Close-up view.
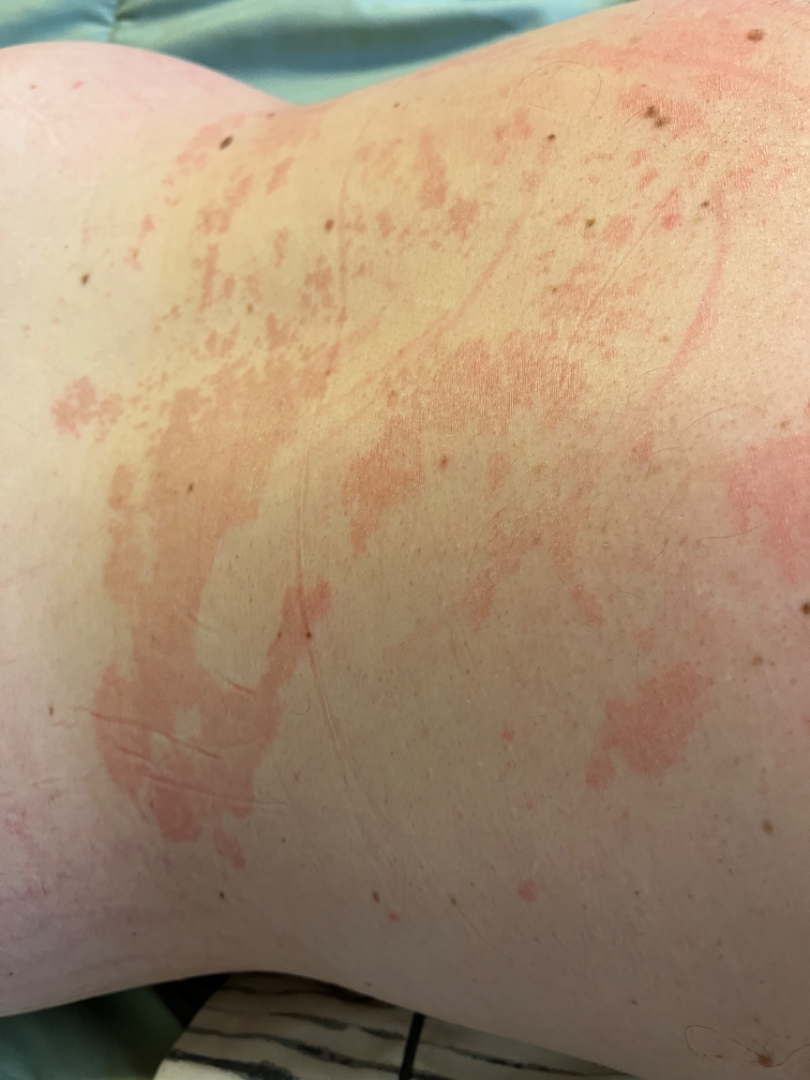The case was indeterminate on photographic review.